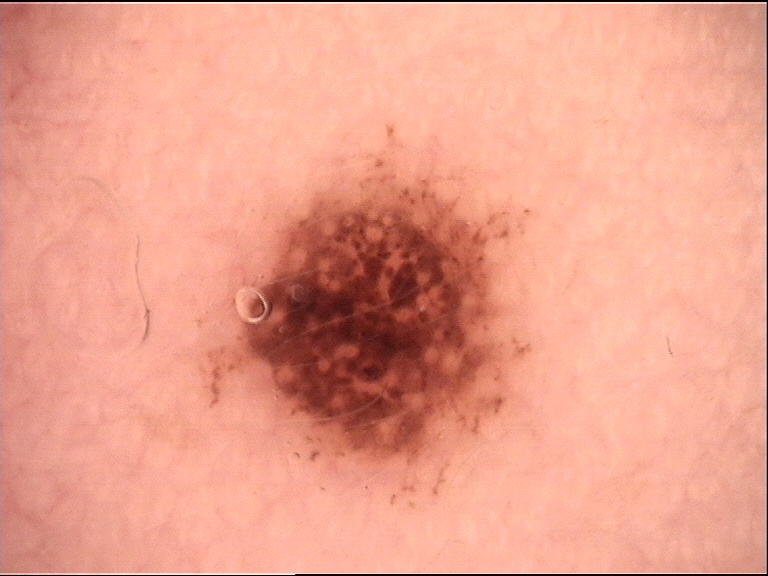The diagnosis was a compound nevus.